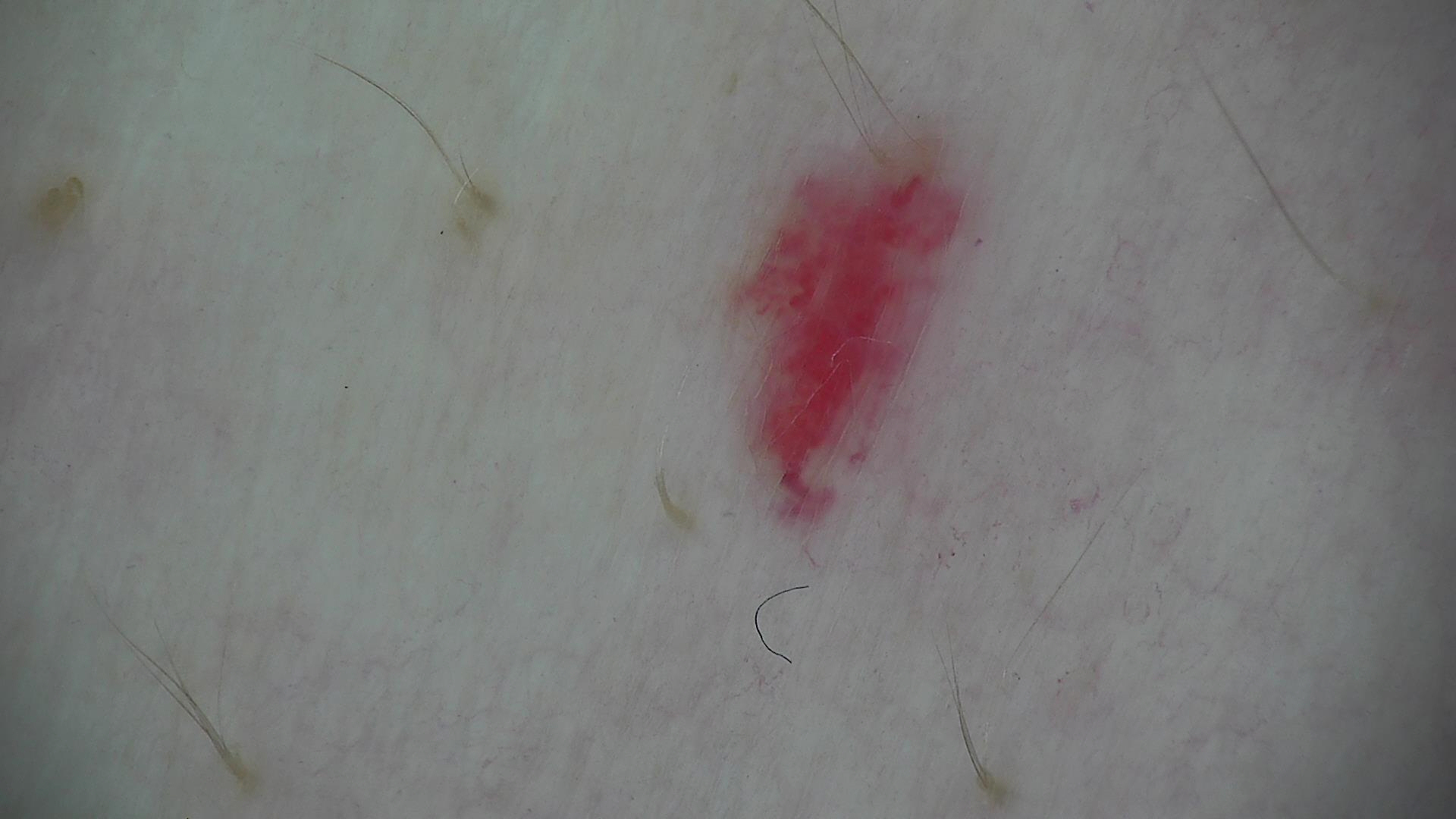modality = dermatoscopy, subtype = vascular, label = hemangioma (expert consensus).